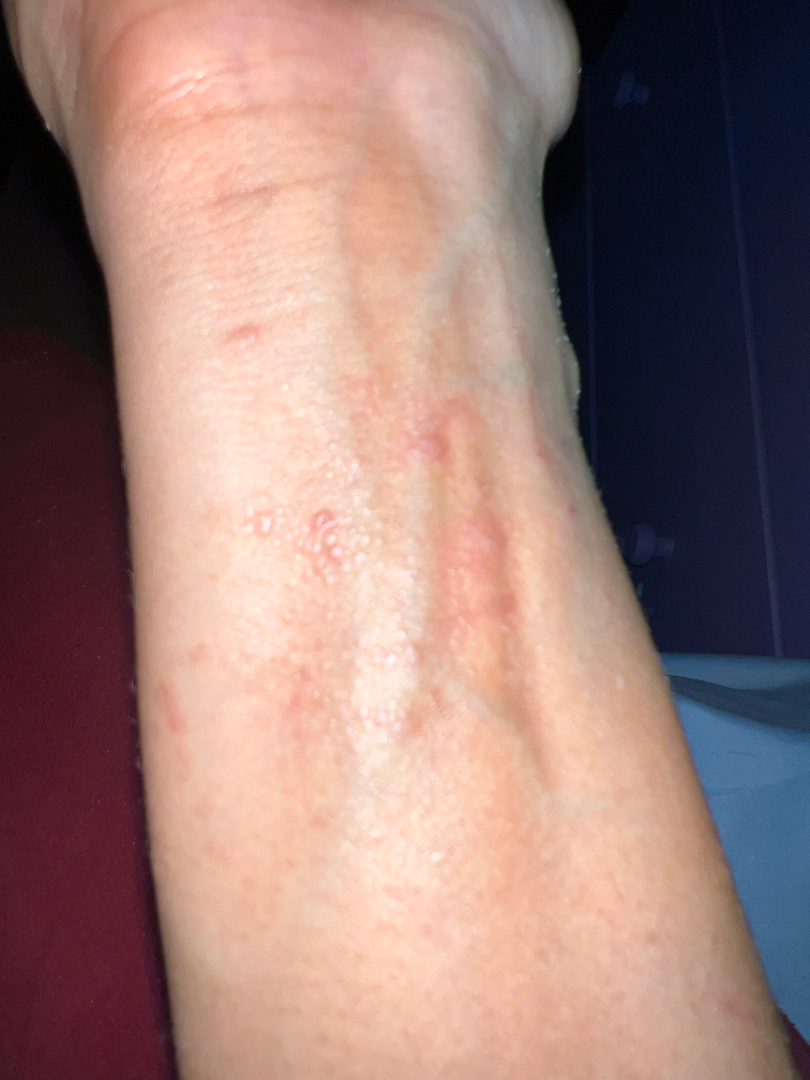Clinical context:
Associated systemic symptoms include joint pain. The patient indicates bleeding, itching and bothersome appearance. The photo was captured at an angle. Skin tone: Fitzpatrick skin type IV; human graders estimated Monk Skin Tone 4 (US pool) or 3 (India pool). Texture is reported as rough or flaky and raised or bumpy. The condition has been present for more than five years. The top or side of the foot, leg and arm are involved.
Assessment:
Single-reviewer assessment: the leading impression is Allergic Contact Dermatitis; also raised was Lichen planus/lichenoid eruption.